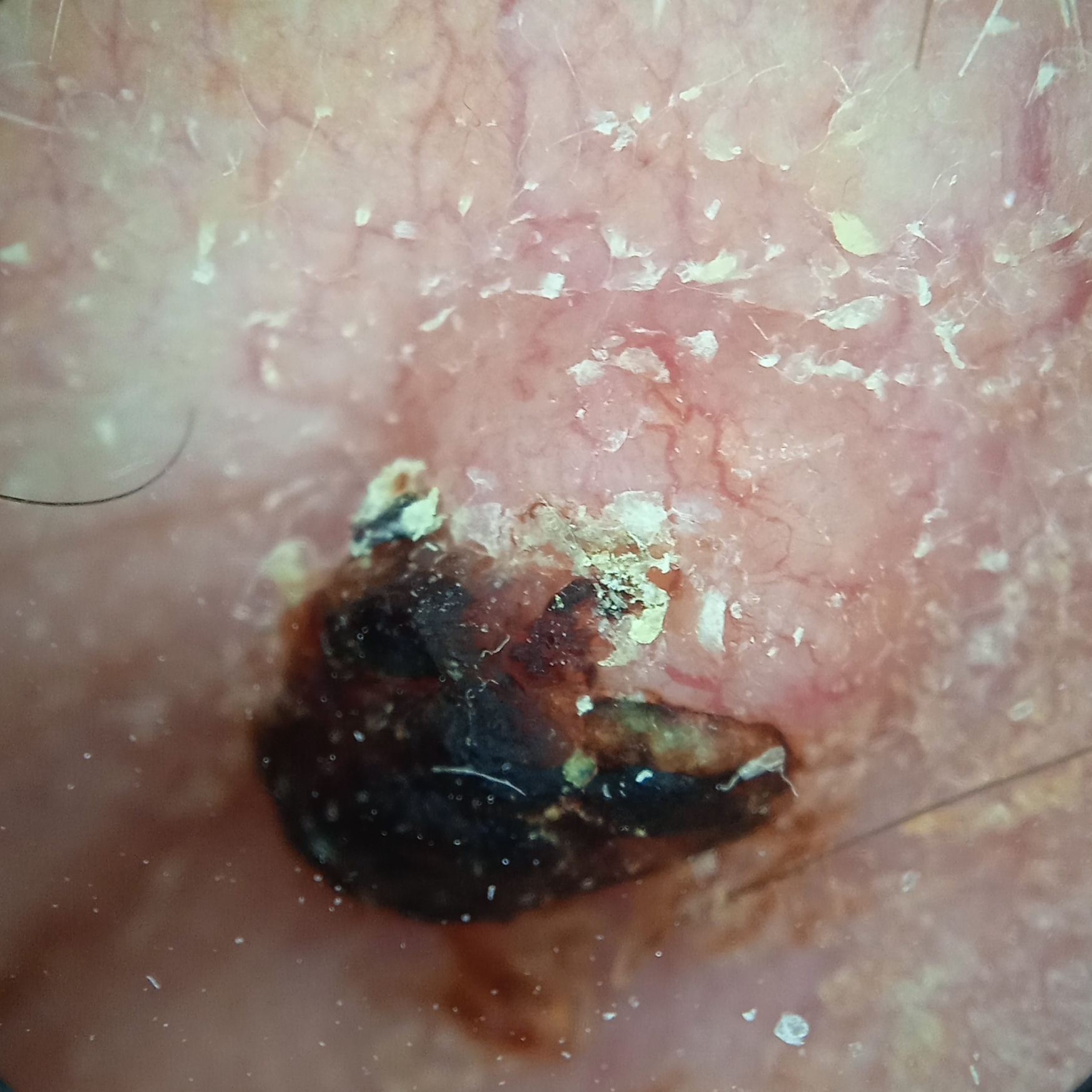A male patient age 83.
The referring clinician suspected basal cell carcinoma.
A dermoscopy image of a skin lesion.
By self-report, no sunbed use and no prior organ transplant.
Histopathologically confirmed as a basal cell carcinoma, following excision, with tumor thickness 2.7 mm.